The photograph is a close-up of the affected area: 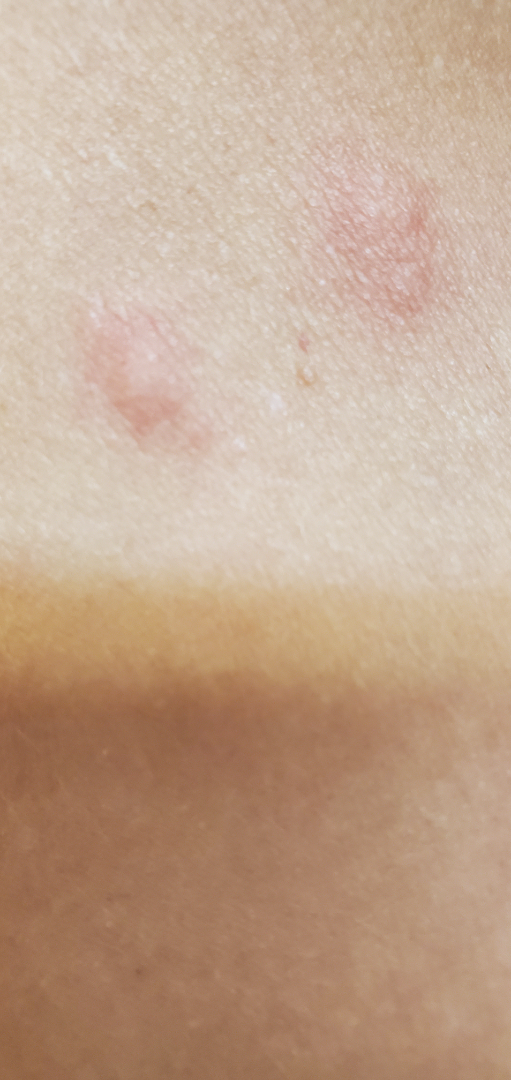Review: No differential diagnosis could be assigned on photographic review.